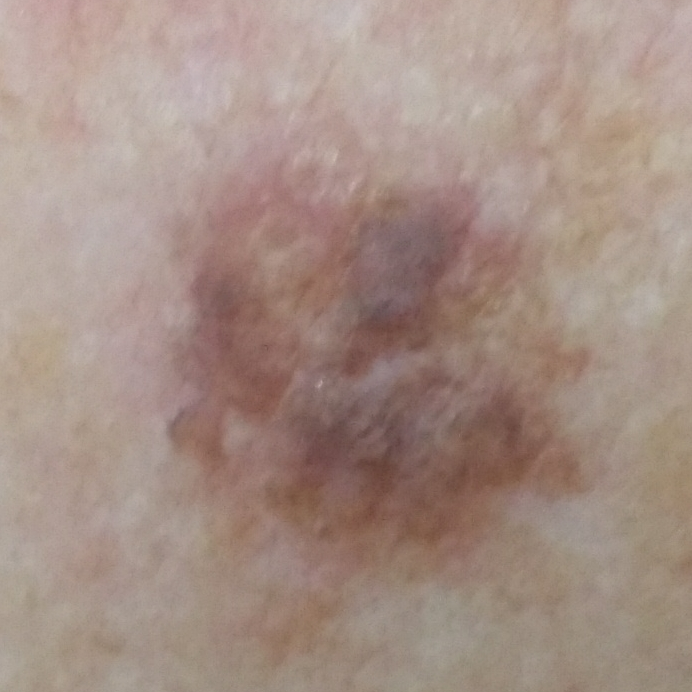* subject — female, in their 70s
* modality — clinical photo
* region — the face
* patient-reported symptoms — elevation
* diagnostic label — seborrheic keratosis (biopsy-proven)